A dermoscopic image of a skin lesion.
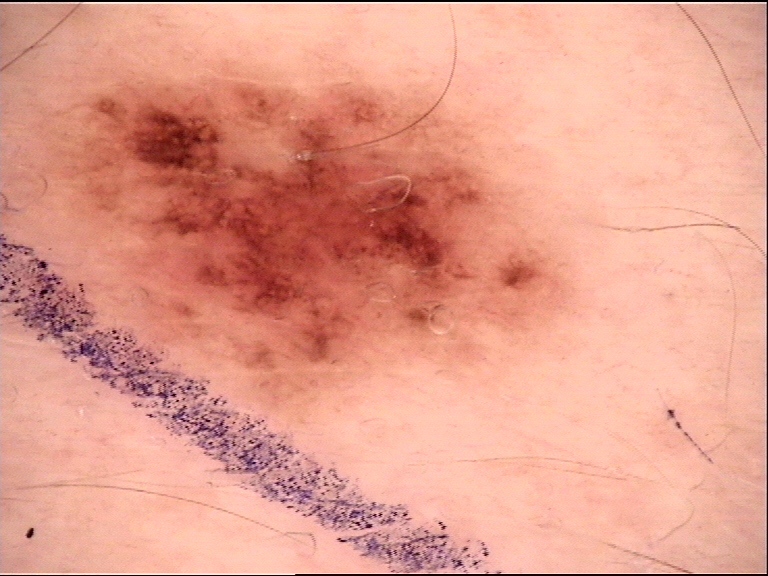Consistent with a benign lesion — a dysplastic junctional nevus.